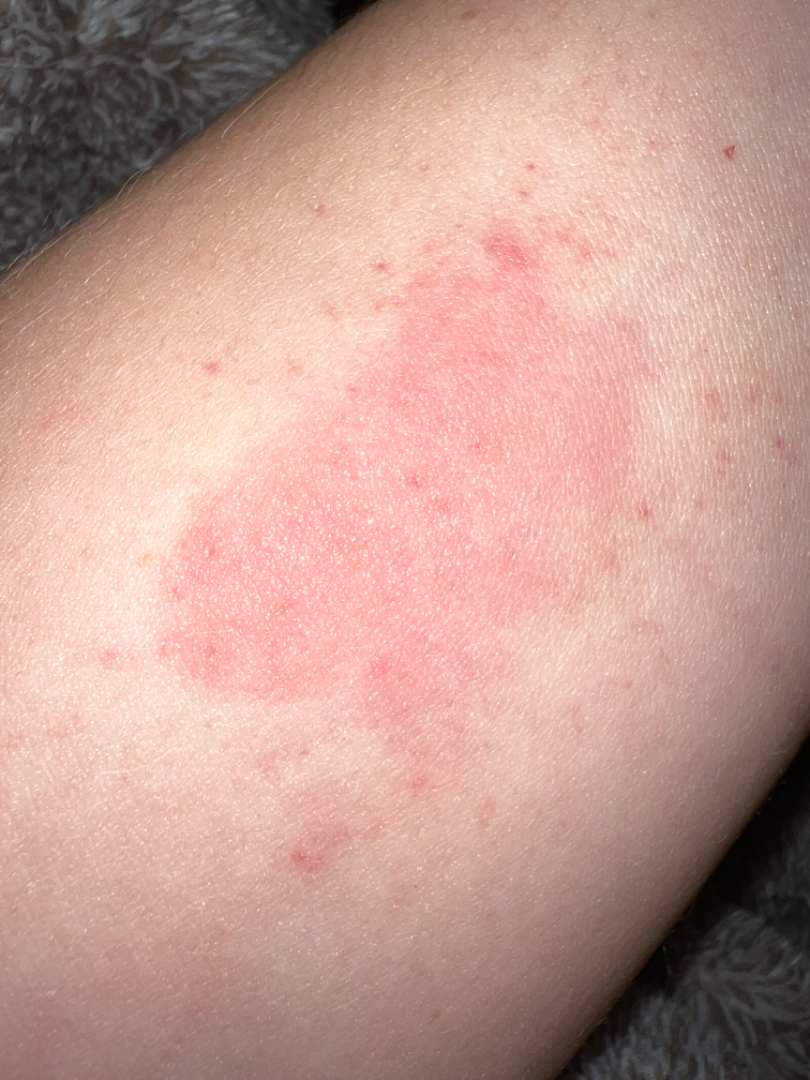Review:
On remote dermatologist review: the impression was split between Eczema, Hypersensitivity and Allergic Contact Dermatitis.